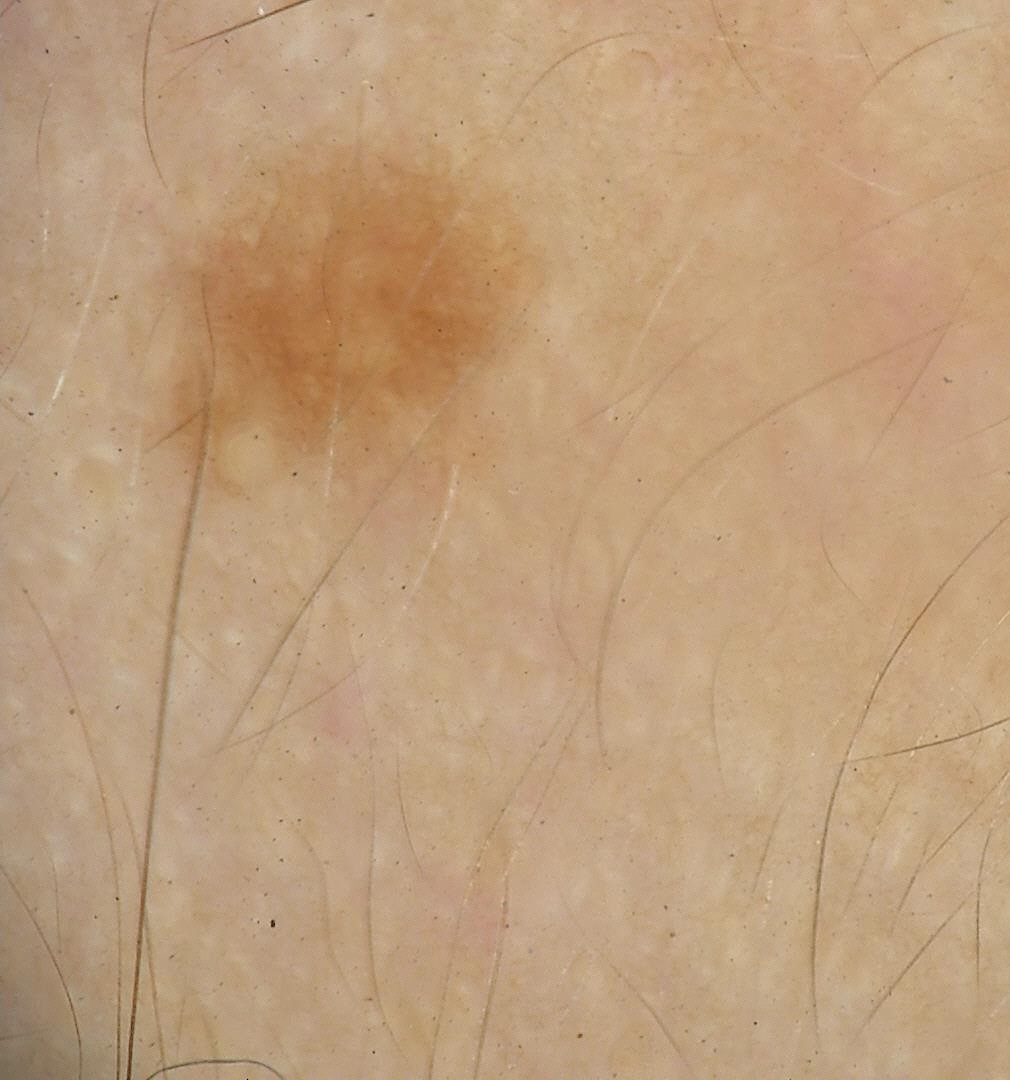Conclusion:
The diagnostic label was a solar lentigo.